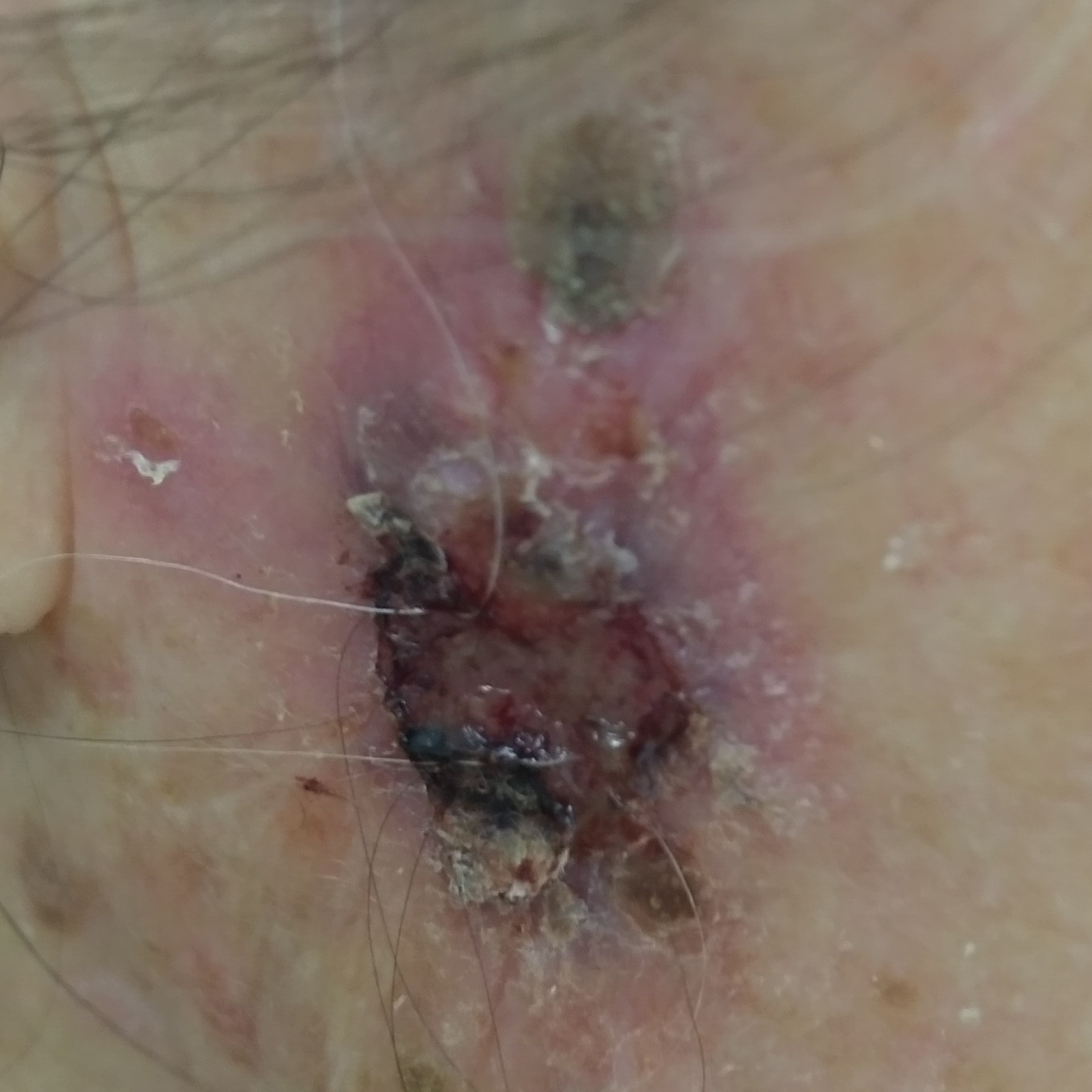Case:
* subject: female, 85 years of age
* modality: smartphone clinical photo
* patient-reported symptoms: elevation, bleeding, change in appearance, growth / no itching, no pain
* diagnostic label: basal cell carcinoma (biopsy-proven)